Female contributor, age 18–29 · reported lesion symptoms include burning, bothersome appearance and enlargement · the lesion involves the top or side of the foot · the patient reported no systemic symptoms · self-categorized by the patient as a rash · an image taken at an angle · reported duration is about one day · texture is reported as flat:
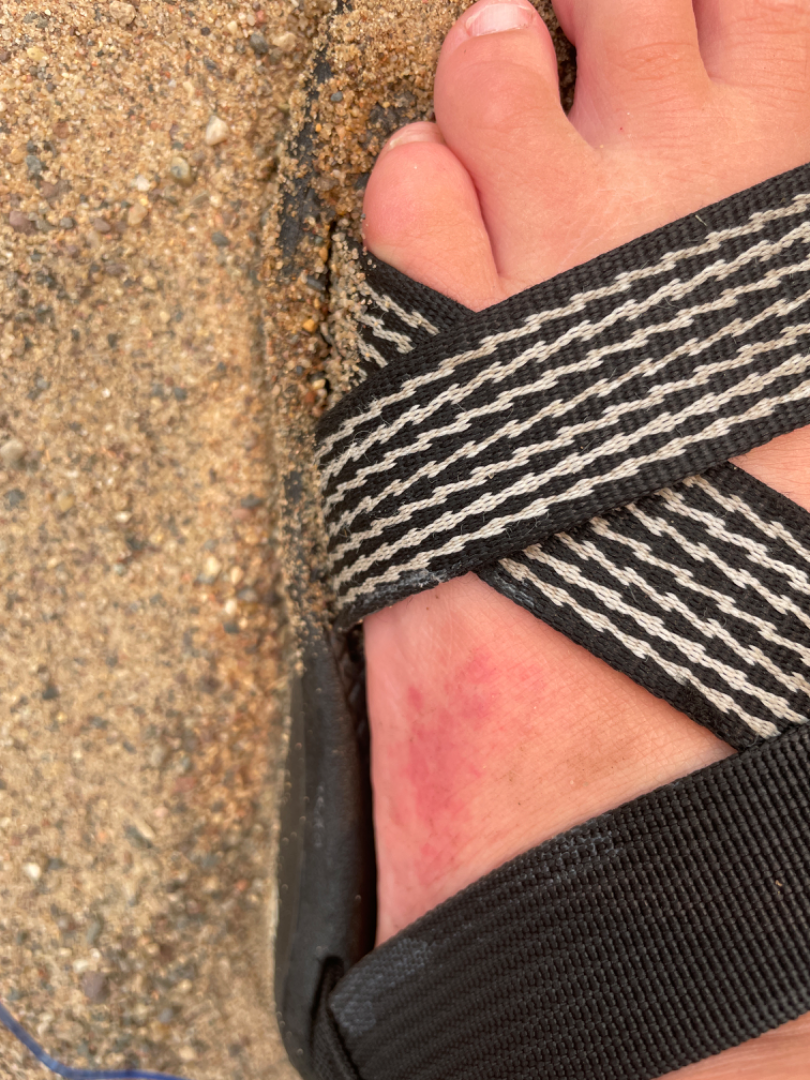No differential diagnosis could be assigned on photographic review.